Female patient, age 50–59; this image was taken at an angle; located on the front of the torso:
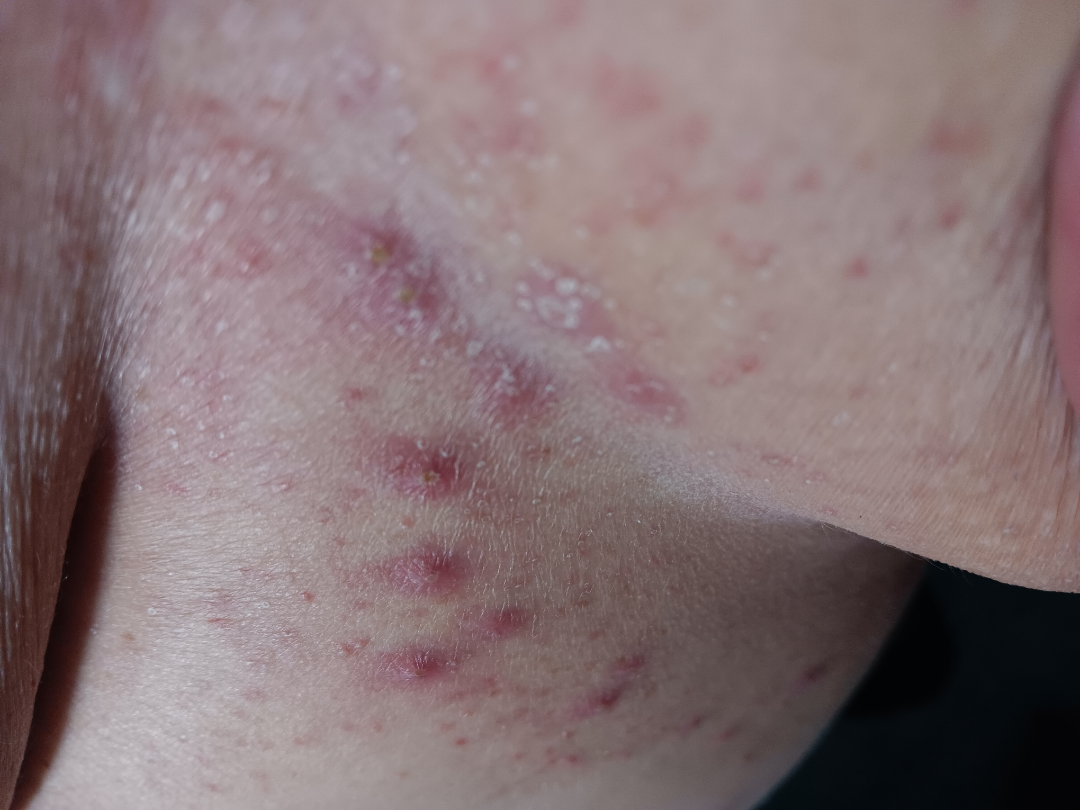  symptoms:
    - pain
    - itching
  texture: raised or bumpy
  patient_category: a rash
  duration: less than one week
  differential:
    Folliculitis: 0.41
    Insect Bite: 0.41
    Localized skin infection: 0.18